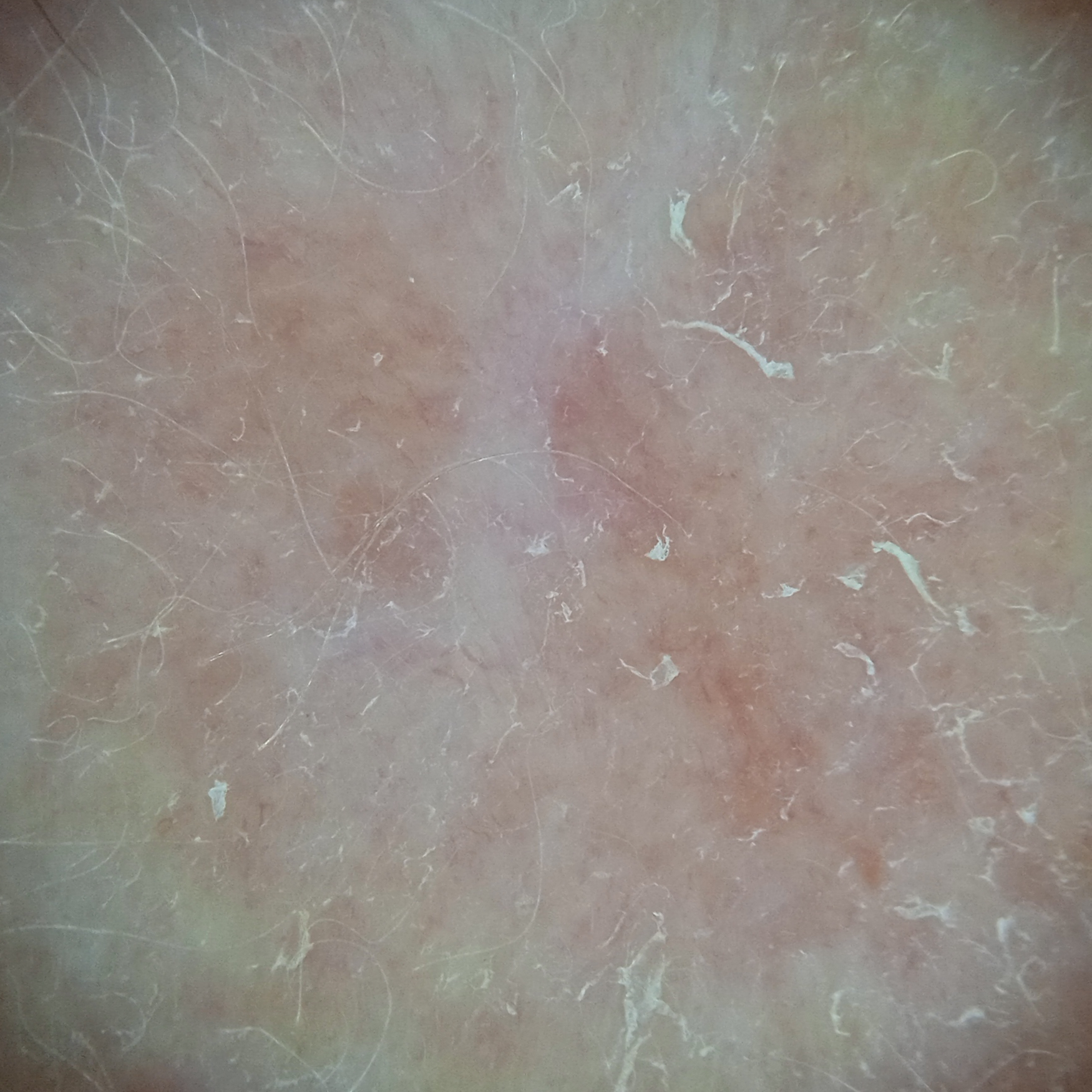Q: What are the relevant risk factors?
A: a family history of skin cancer, a personal history of cancer
Q: How does the patient's skin react to sun?
A: skin tans without first burning
Q: What is the imaging modality?
A: dermatoscopic image
Q: Tell me about the patient.
A: female, age 92
Q: Why was this imaged?
A: clinical suspicion of basal cell carcinoma
Q: Where is the lesion?
A: the face
Q: Lesion size?
A: 11.5 mm
Q: What did the biopsy show?
A: basal cell carcinoma (biopsy-proven)